Dermoscopy of a skin lesion — 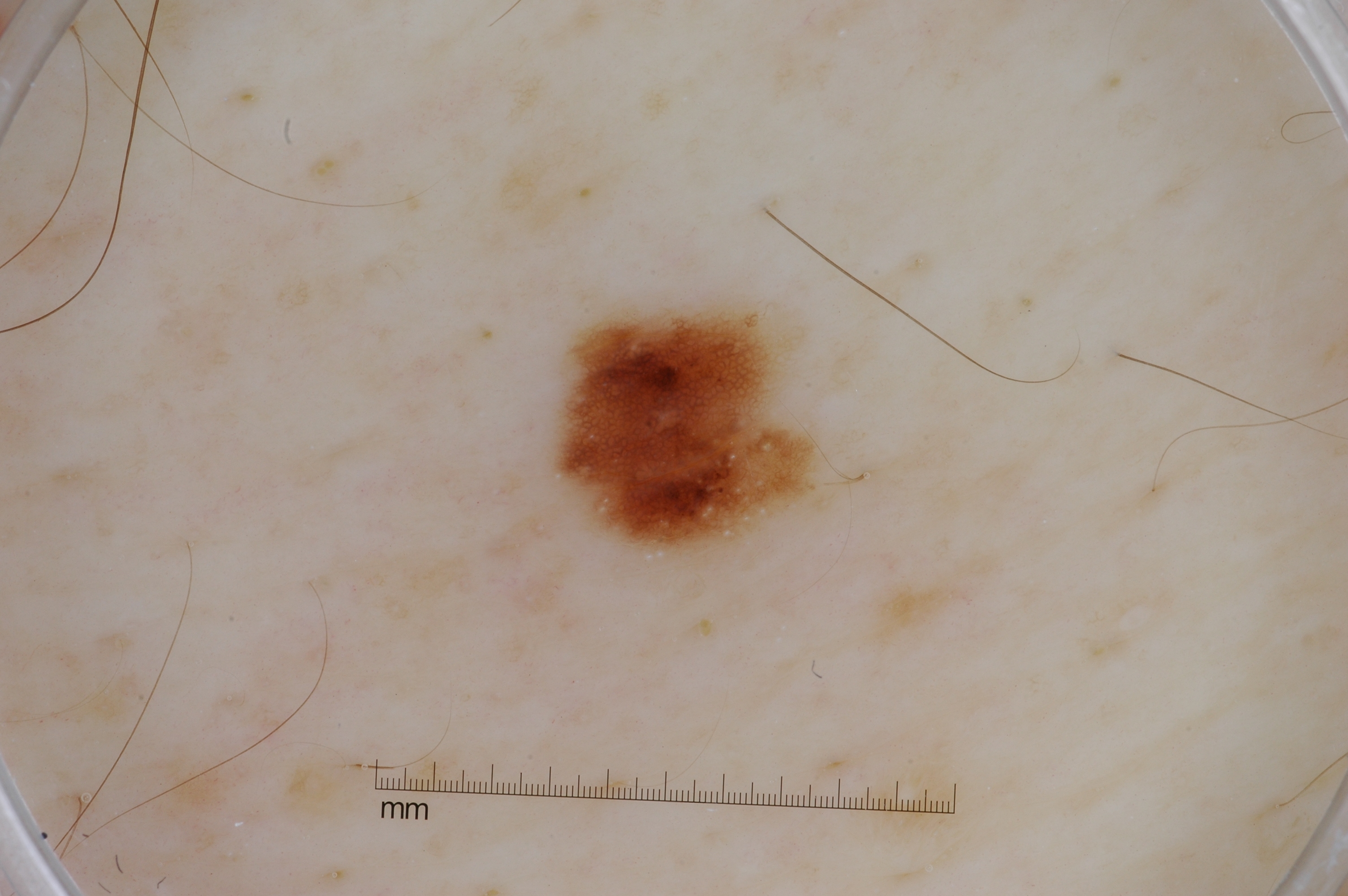dermoscopic features: milia-like cysts and pigment network; lesion bbox: <box>558, 308, 822, 553</box>; extent: ~4% of the field; diagnostic label: a melanocytic nevus, a benign lesion.